A dermatoscopic image of a skin lesion.
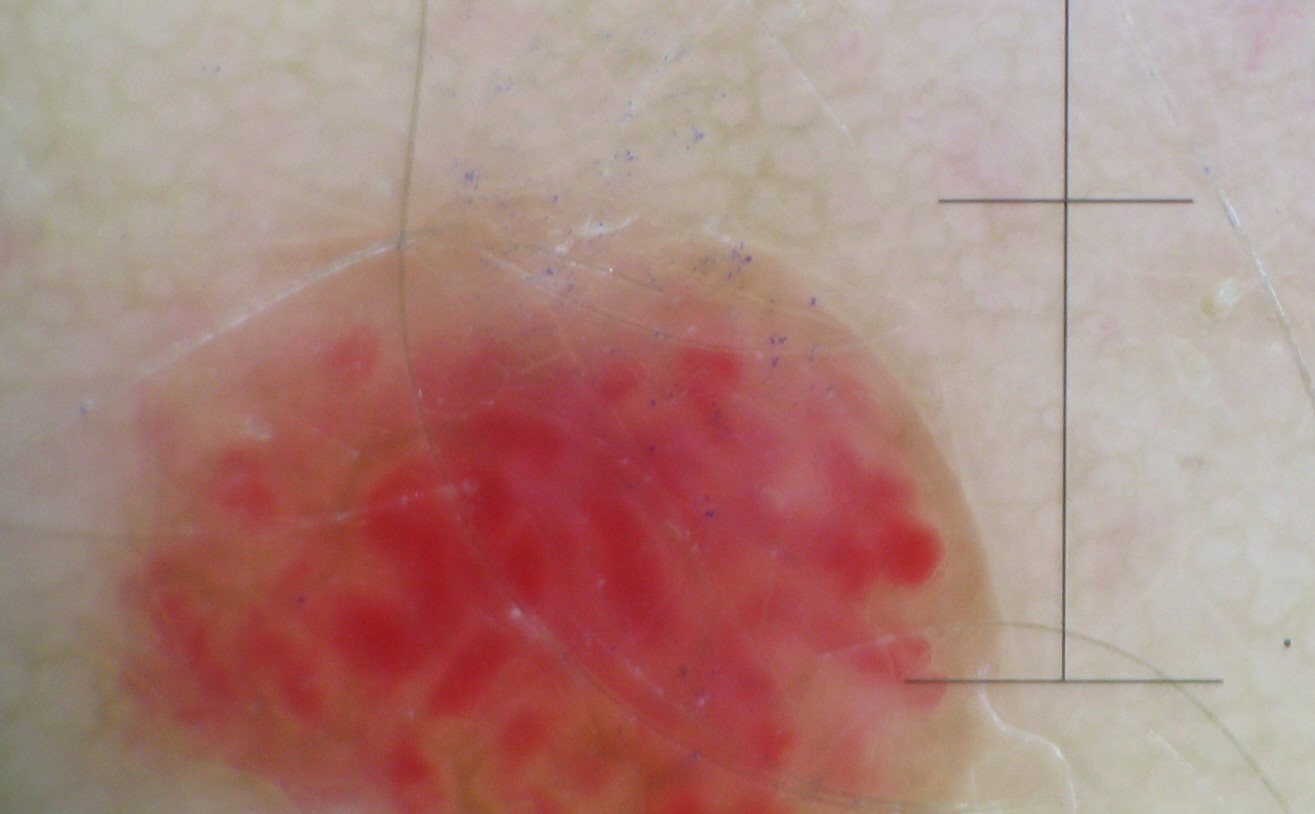Q: How is the lesion classified?
A: vascular
Q: What is the diagnosis?
A: hemangioma (expert consensus)